A dermoscopy image of a single skin lesion: 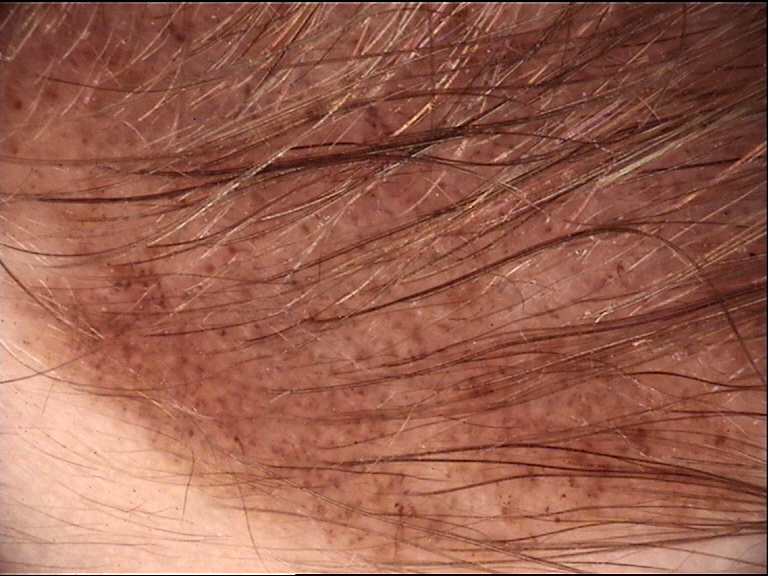Conclusion: The diagnosis was a congenital compound nevus.